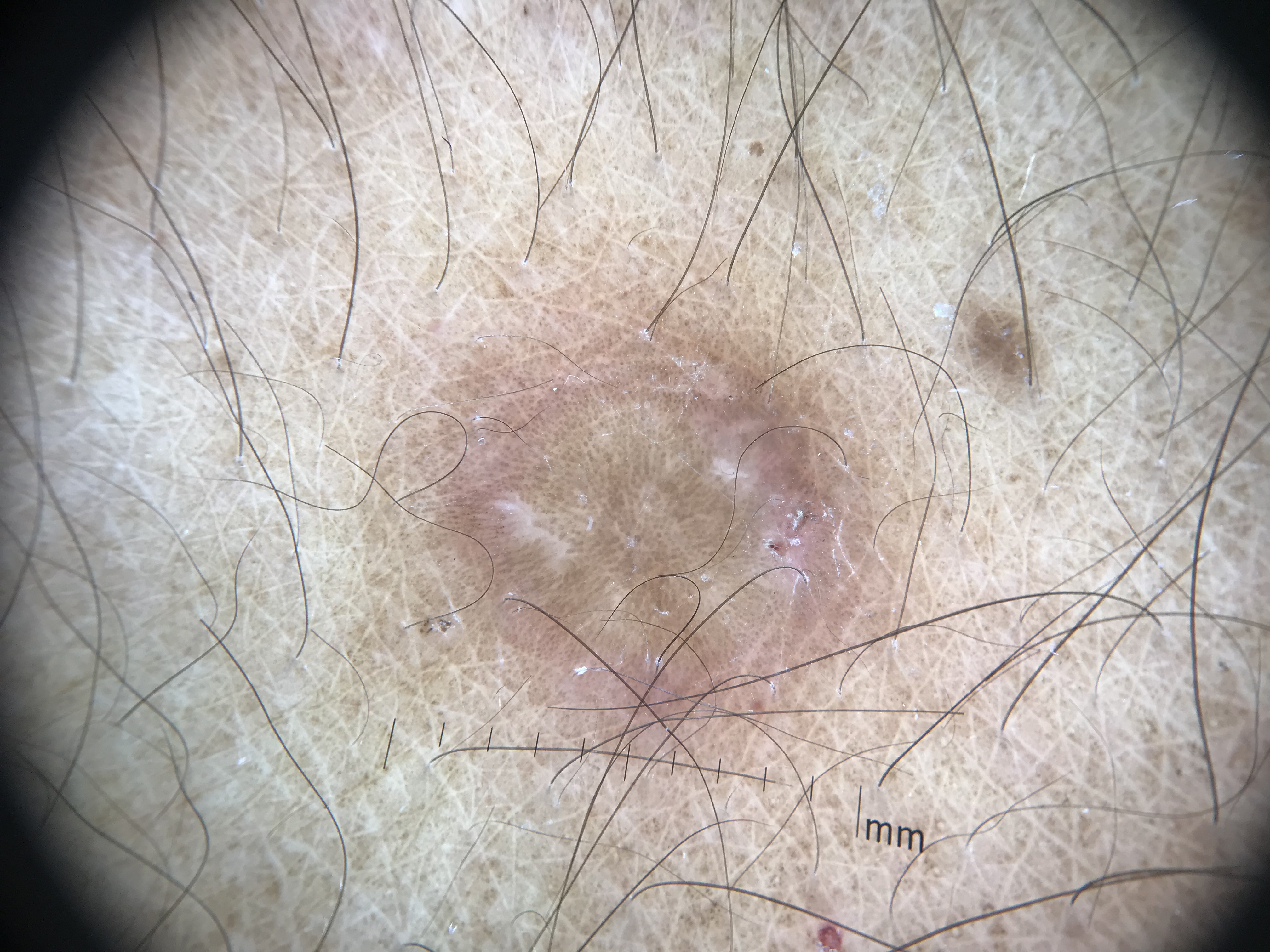assessment = dermatofibroma (expert consensus)